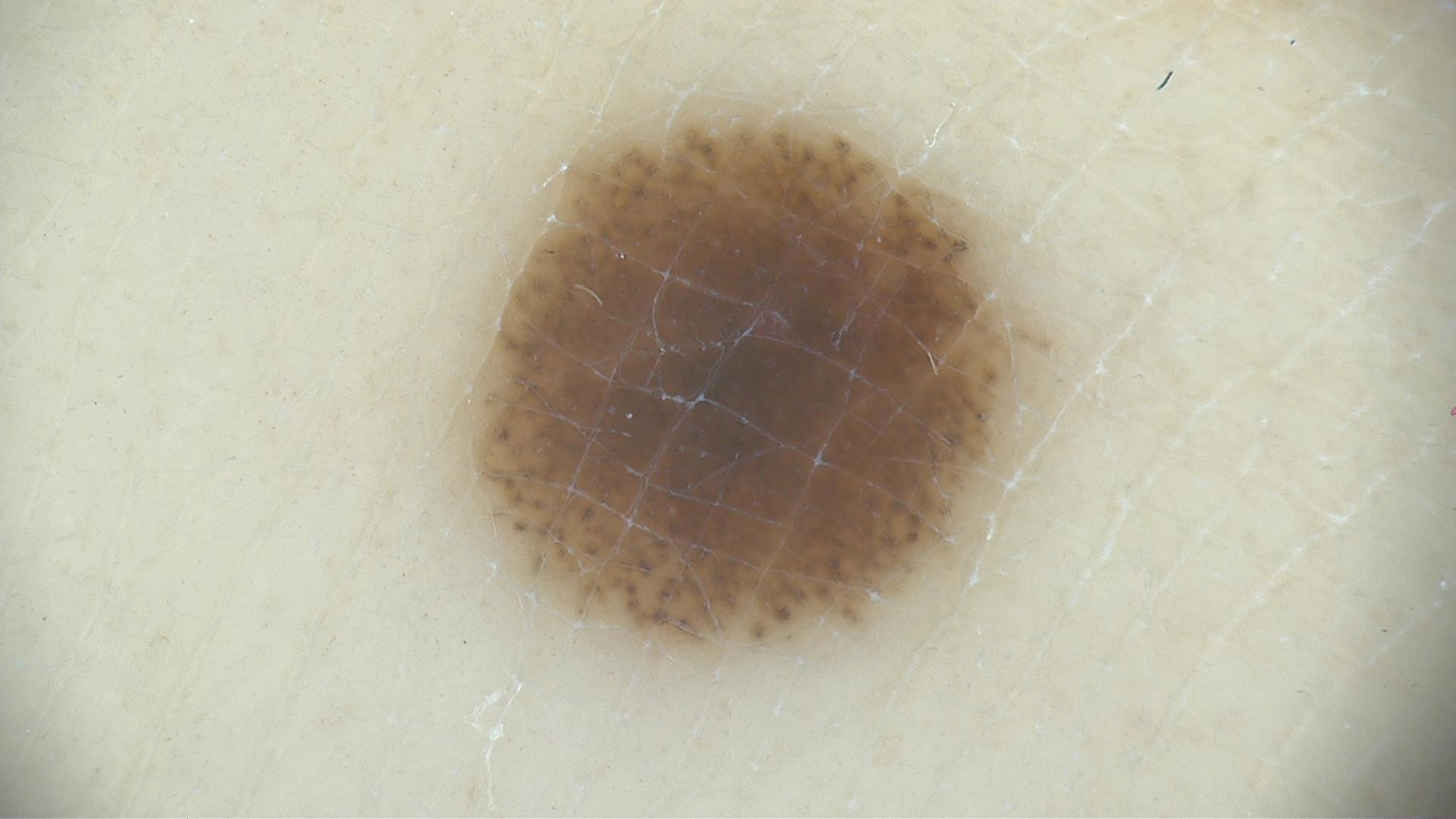  image: dermoscopy
  diagnosis:
    name: dysplastic junctional nevus
    code: jd
    malignancy: benign
    super_class: melanocytic
    confirmation: expert consensus